The subject is a male aged 30–39. The lesion involves the arm. An image taken at an angle:
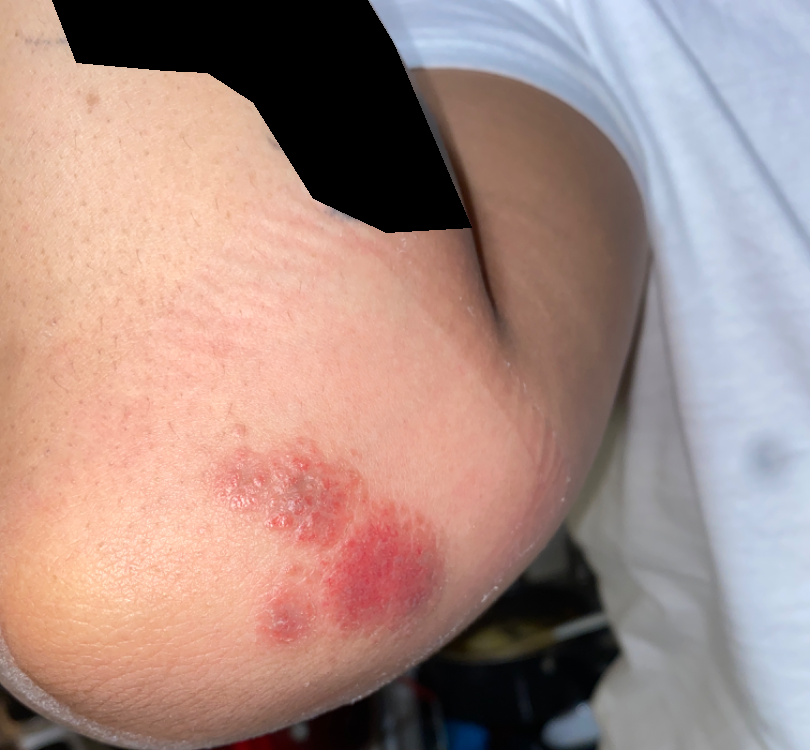diagnostic considerations = reviewed remotely by one dermatologist: the primary impression is Herpes Zoster; possibly Allergic Contact Dermatitis; lower on the differential is Herpes Simplex